Symptoms reported: darkening. Self-categorized by the patient as a rash. Close-up view. Located on the palm and back of the hand. Reported duration is less than one week. The lesion is described as flat: 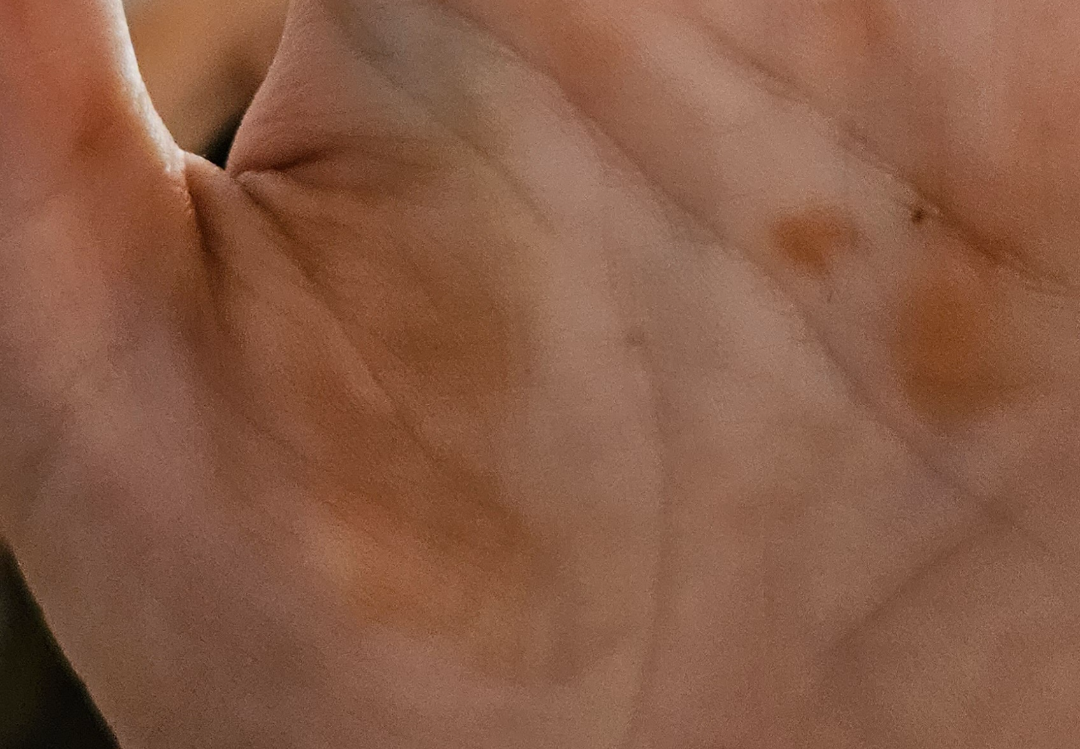Case summary:
- clinical impression · the differential includes Syphilis and Allergic Contact Dermatitis, with no clear leading consideration